Dermoscopy of a skin lesion:
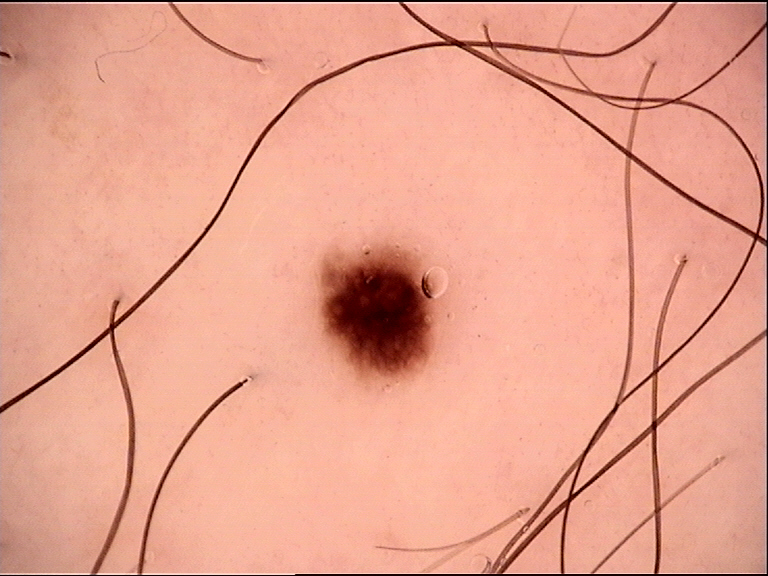Labeled as a dysplastic junctional nevus.